The lesion involves the back of the hand; the patient is a female aged 60–69; the photograph was taken at an angle:
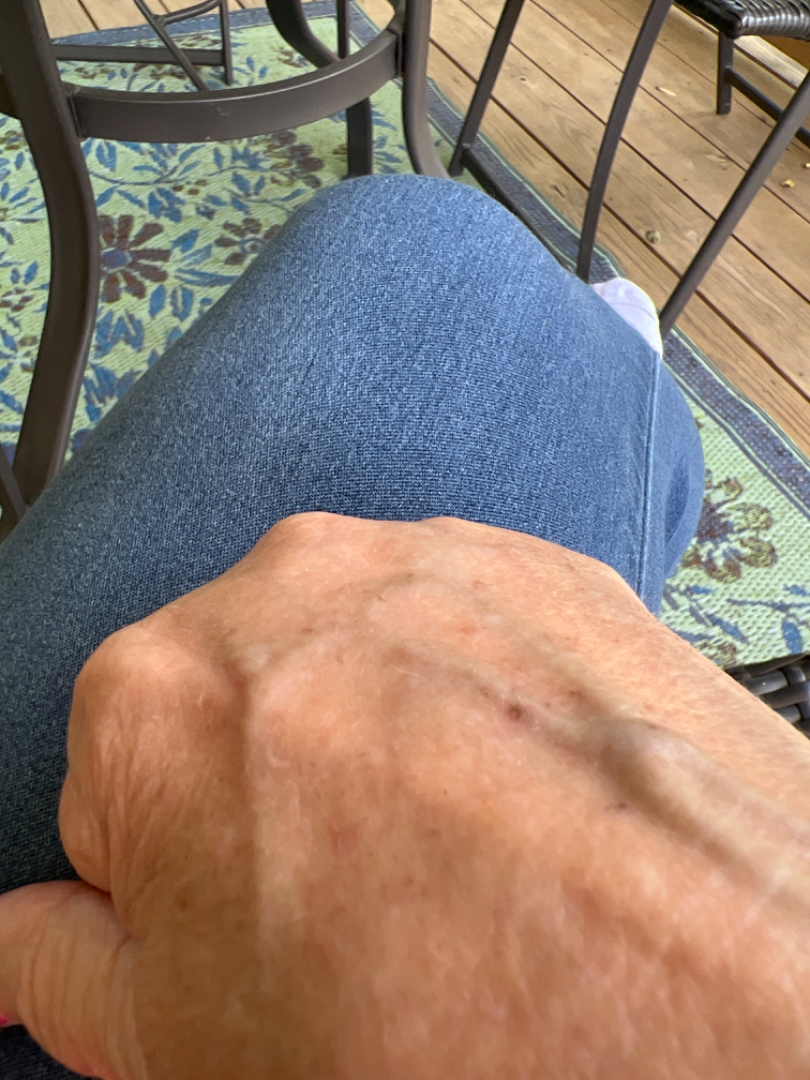On remote review of the image, Actinic Keratosis (most likely).